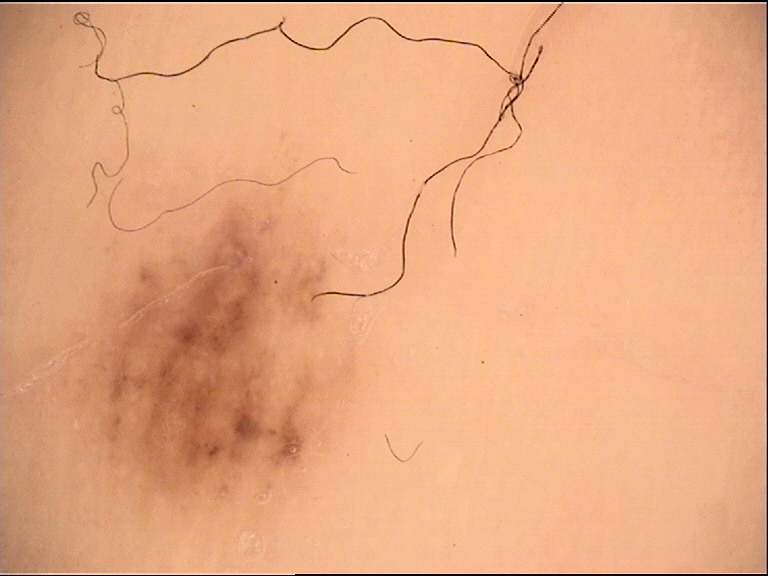A dermatoscopic image of a skin lesion. Classified as a benign lesion — an acral dysplastic junctional nevus.